A dermatoscopic image of a skin lesion.
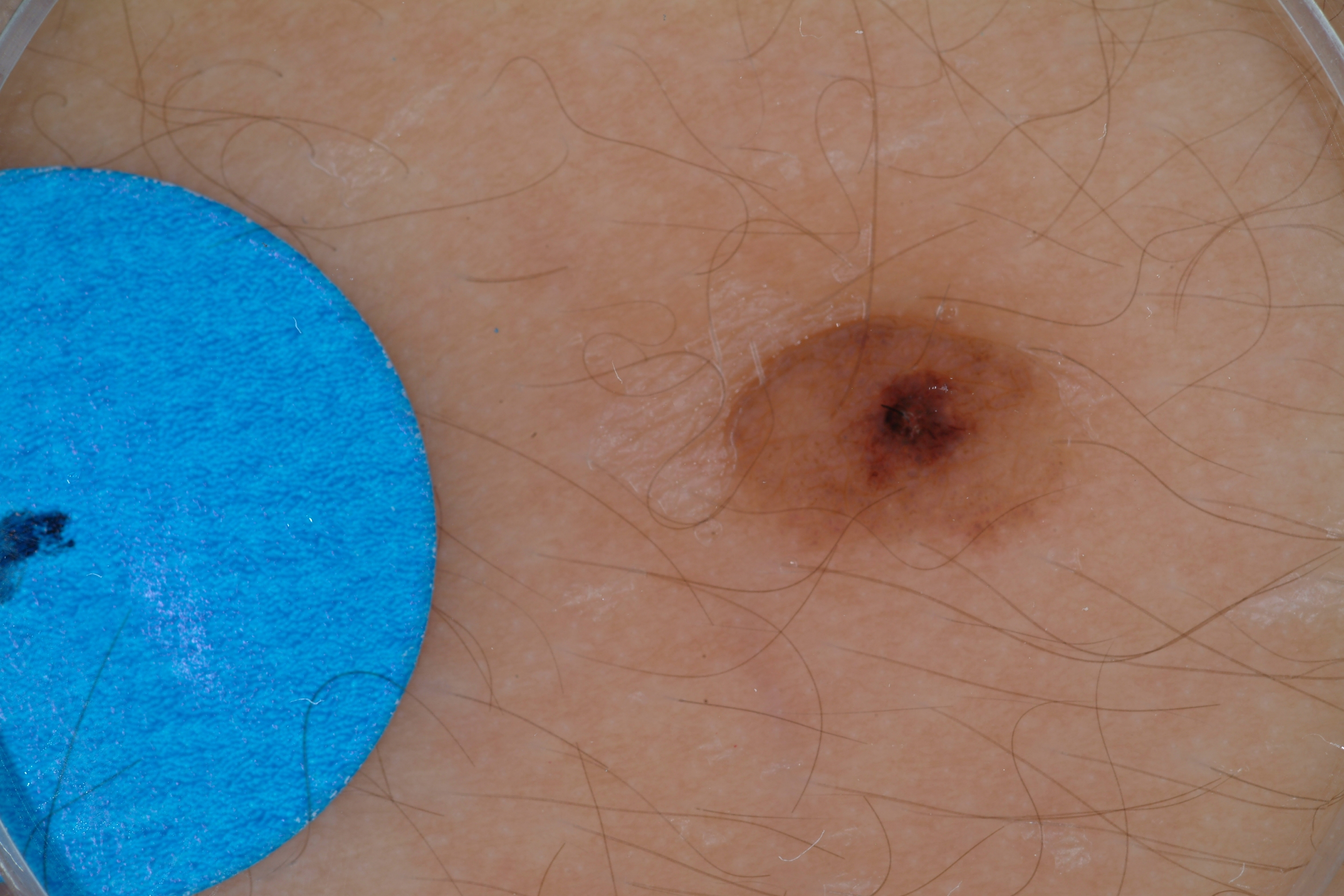Dermoscopic review identifies no globules, milia-like cysts, pigment network, negative network, or streaks. The lesion's extent is 691 302 1089 576. The lesion is small relative to the field of view. Consistent with a melanocytic nevus, a benign lesion.